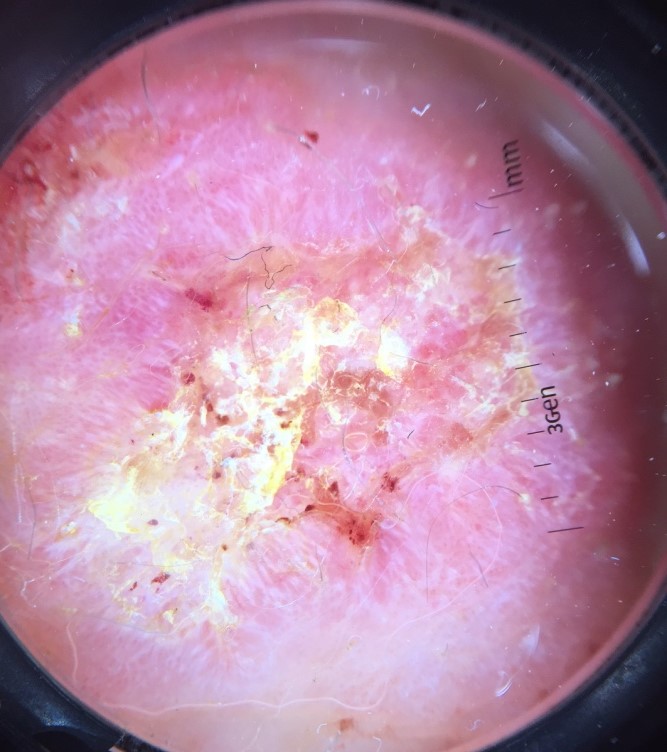{"image": "dermoscopy", "diagnosis": {"name": "squamous cell carcinoma", "code": "scc", "malignancy": "malignant", "super_class": "non-melanocytic", "confirmation": "histopathology"}}